A dermoscopic close-up of a skin lesion.
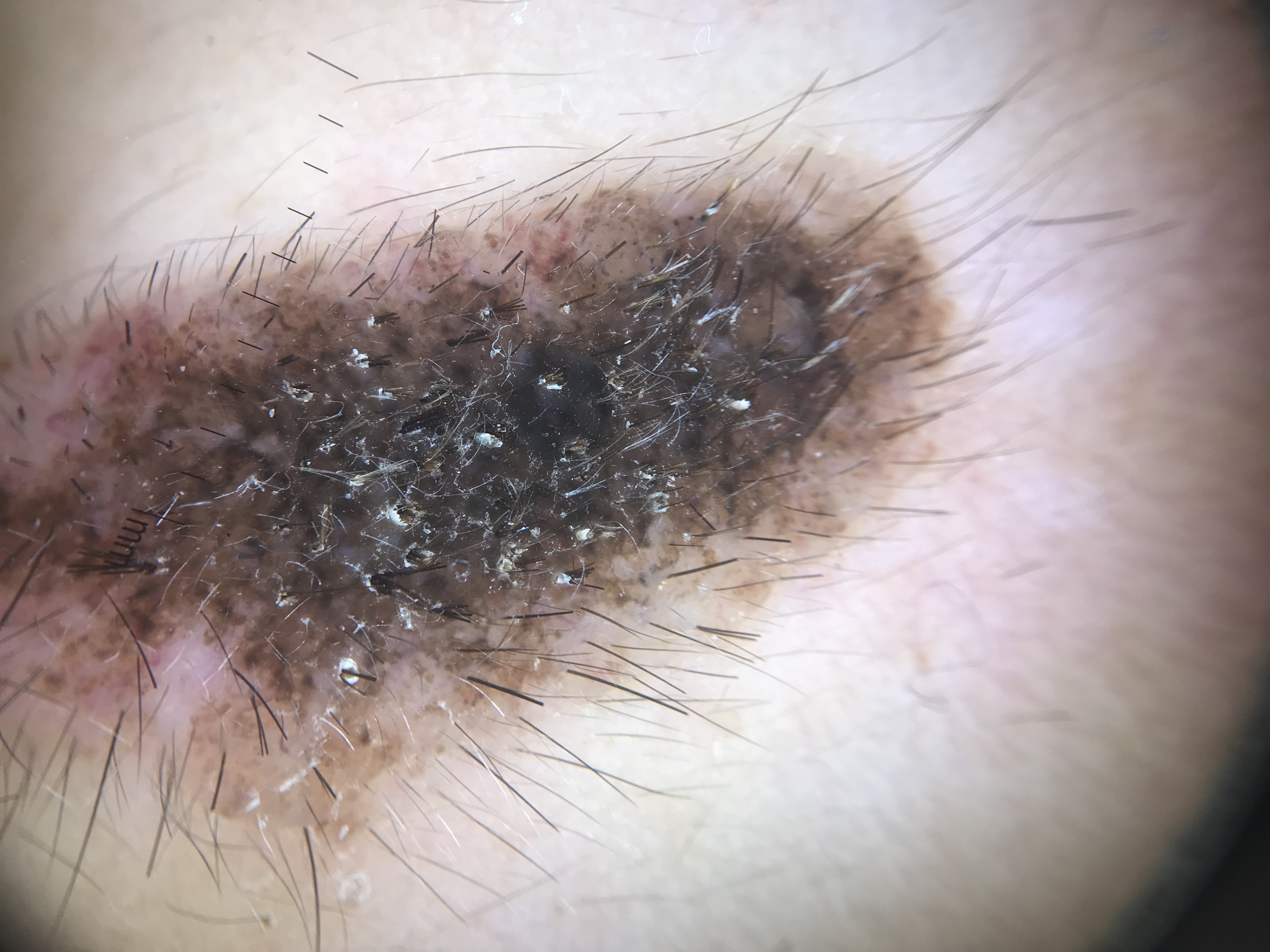The diagnosis was a banal lesion — a congenital compound nevus.